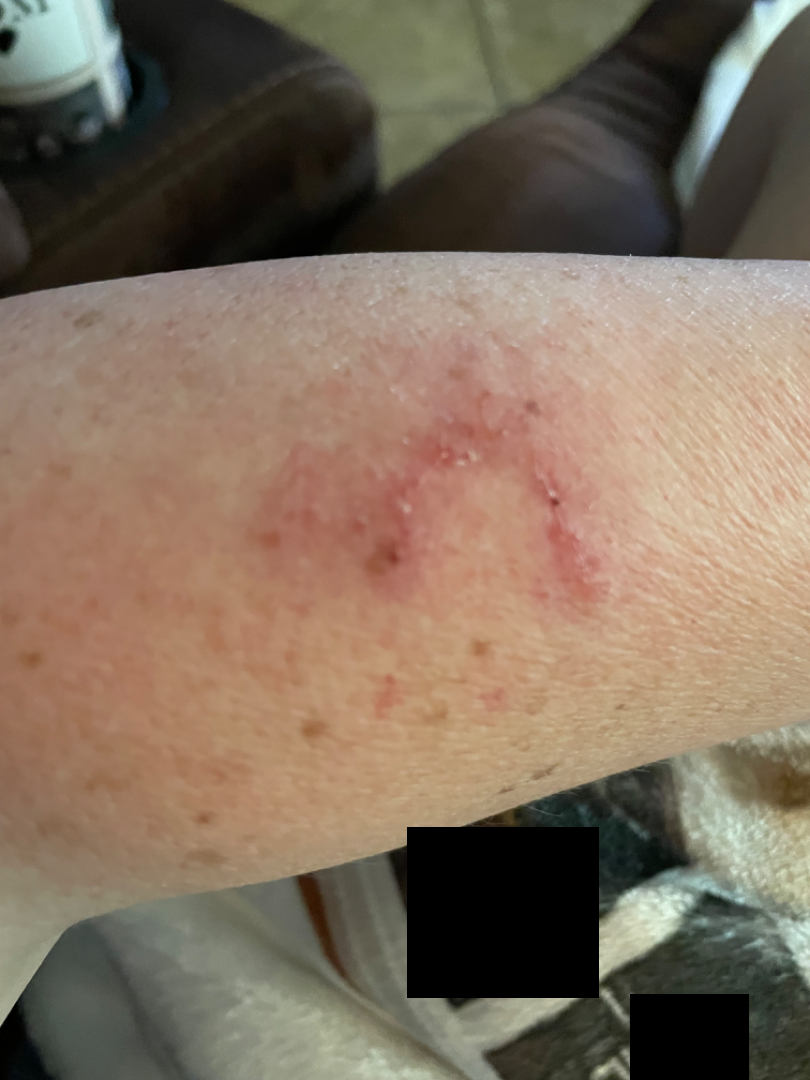Close-up view. Lay reviewers estimated Monk Skin Tone 2. The lesion is associated with bleeding, enlargement, itching and bothersome appearance. The affected area is the arm. Female contributor, age 50–59. No relevant systemic symptoms. Self-categorized by the patient as a rash. Irritant Contact Dermatitis and Tinea were considered with similar weight; a more distant consideration is Eczema; less likely is Cutaneous lupus; less probable is Psoriasis.